A patient in their 60s · a clinical photo of a skin lesion taken with a smartphone:
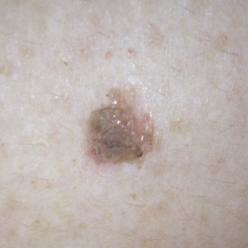The consensus clinical diagnosis was a benign skin lesion — a seborrheic keratosis.